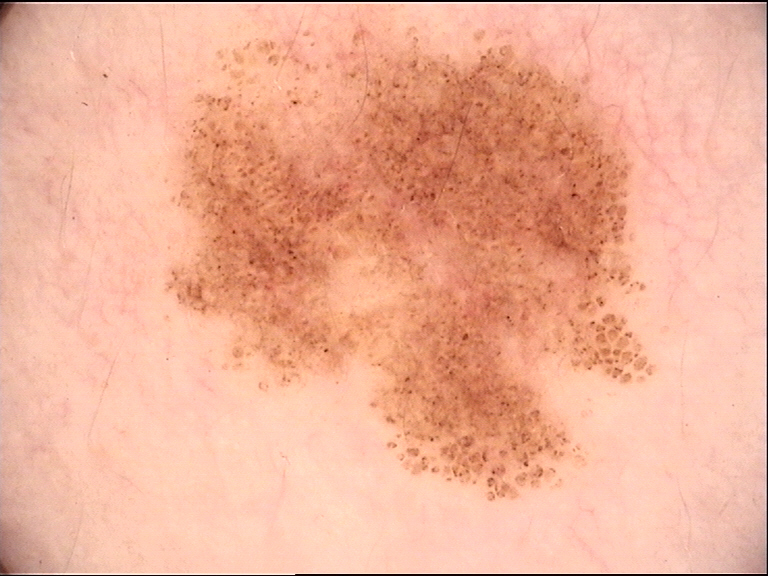Diagnosed as a dysplastic junctional nevus.